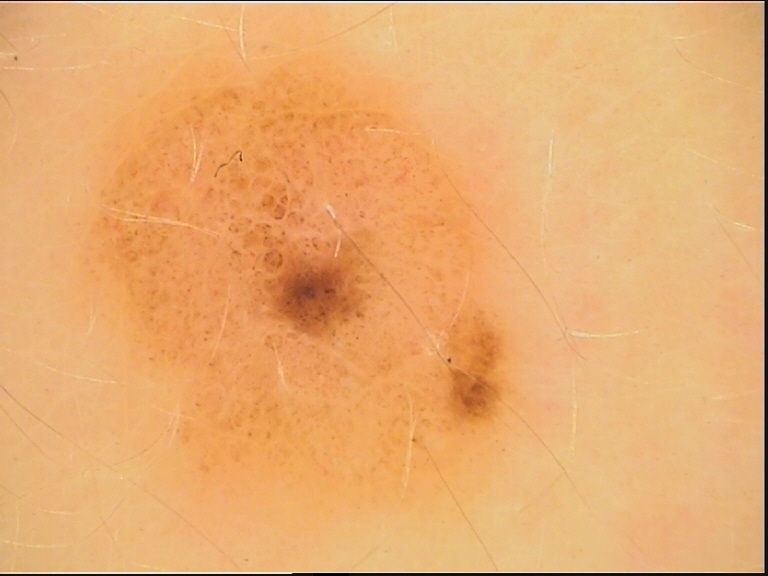Labeled as a compound nevus.